The affected area is the head or neck. Reported duration is one to four weeks. No relevant lesion symptoms reported. The contributor reports the lesion is fluid-filled. The photograph was taken at a distance. The patient considered this a rash. The subject is a male aged 18–29.
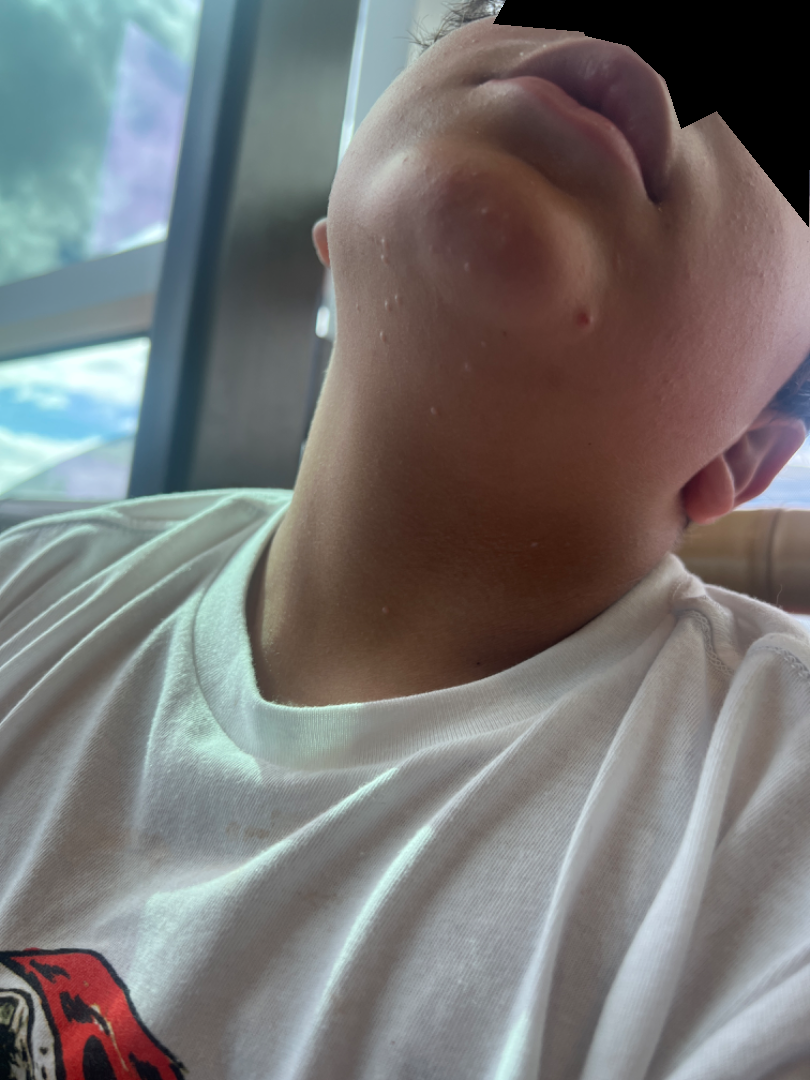assessment=indeterminate.